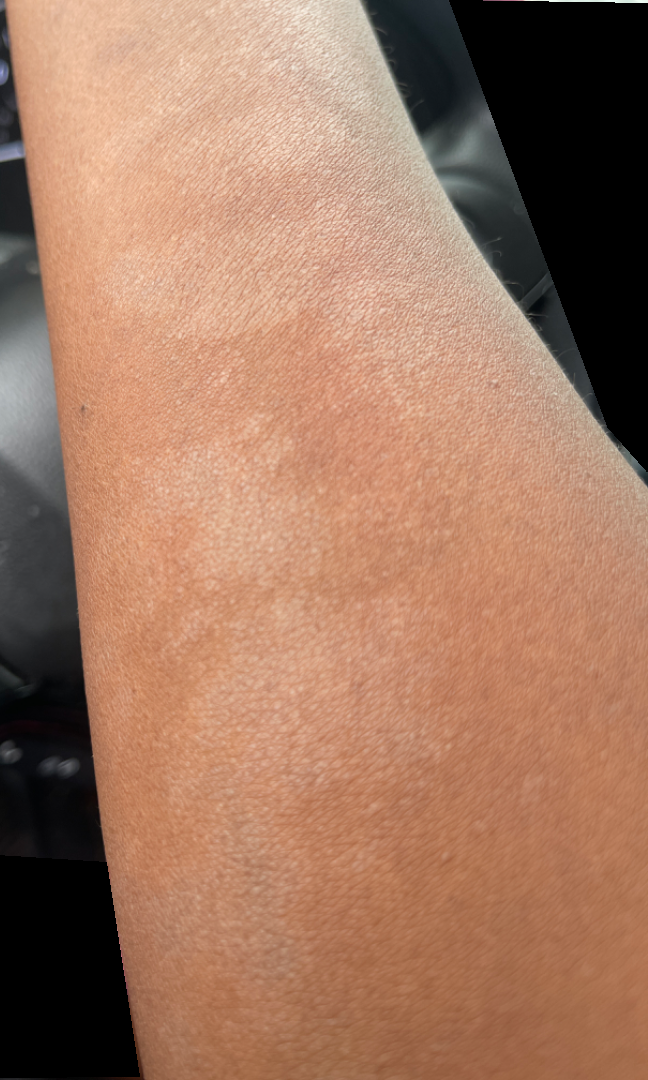Assessment:
On independent review by the dermatologists, the differential, in no particular order, includes Pityriasis alba and Vitiligo; possibly Post-Inflammatory hypopigmentation.